A close-up photograph. Located on the back of the hand and top or side of the foot. Female subject, age 18–29:
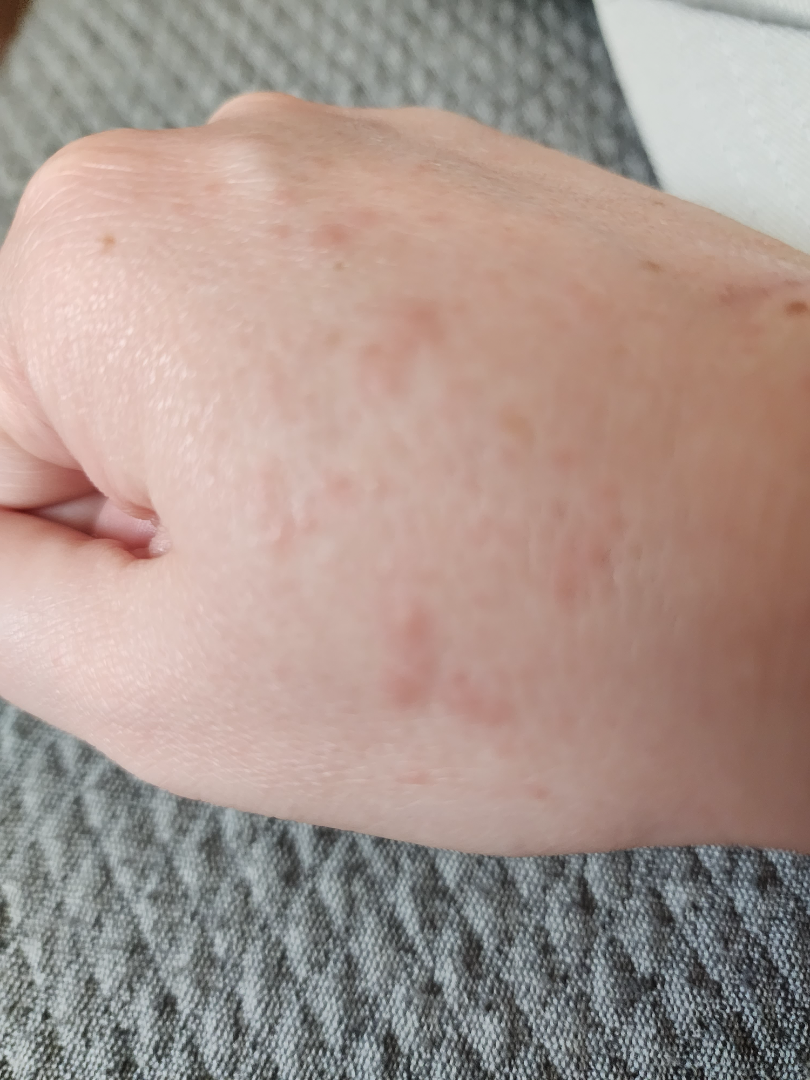Q: What was the assessment?
A: unable to determine
Q: Patient's own categorization?
A: a rash
Q: Texture?
A: flat and raised or bumpy
Q: Constitutional symptoms?
A: none reported
Q: Fitzpatrick or Monk tone?
A: self-reported Fitzpatrick I
Q: How long has this been present?
A: about one day